The lesion involves the leg. Close-up view:
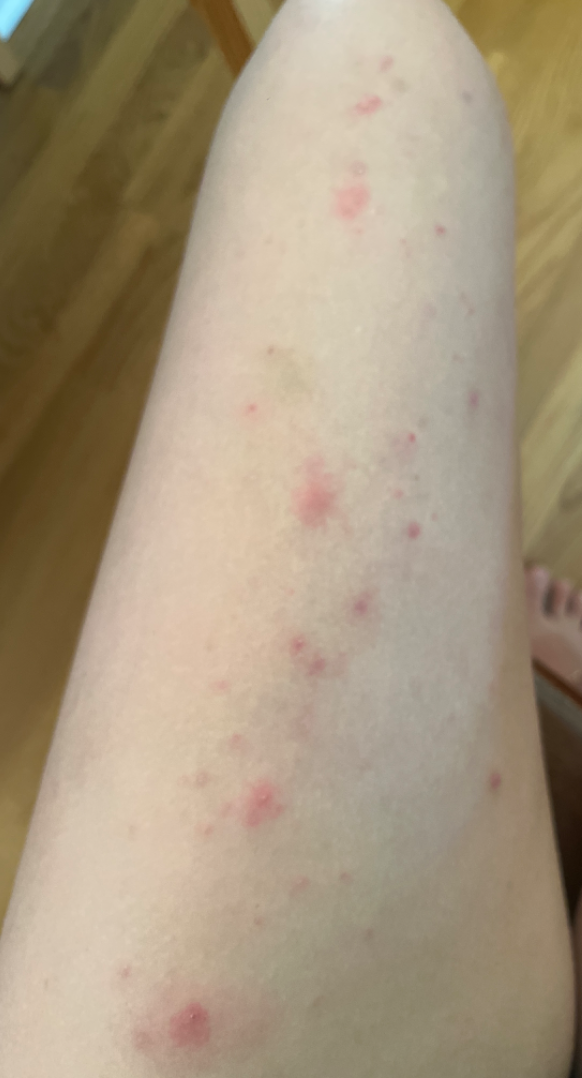Consistent with Folliculitis.